A dermoscopic photograph of a skin lesion.
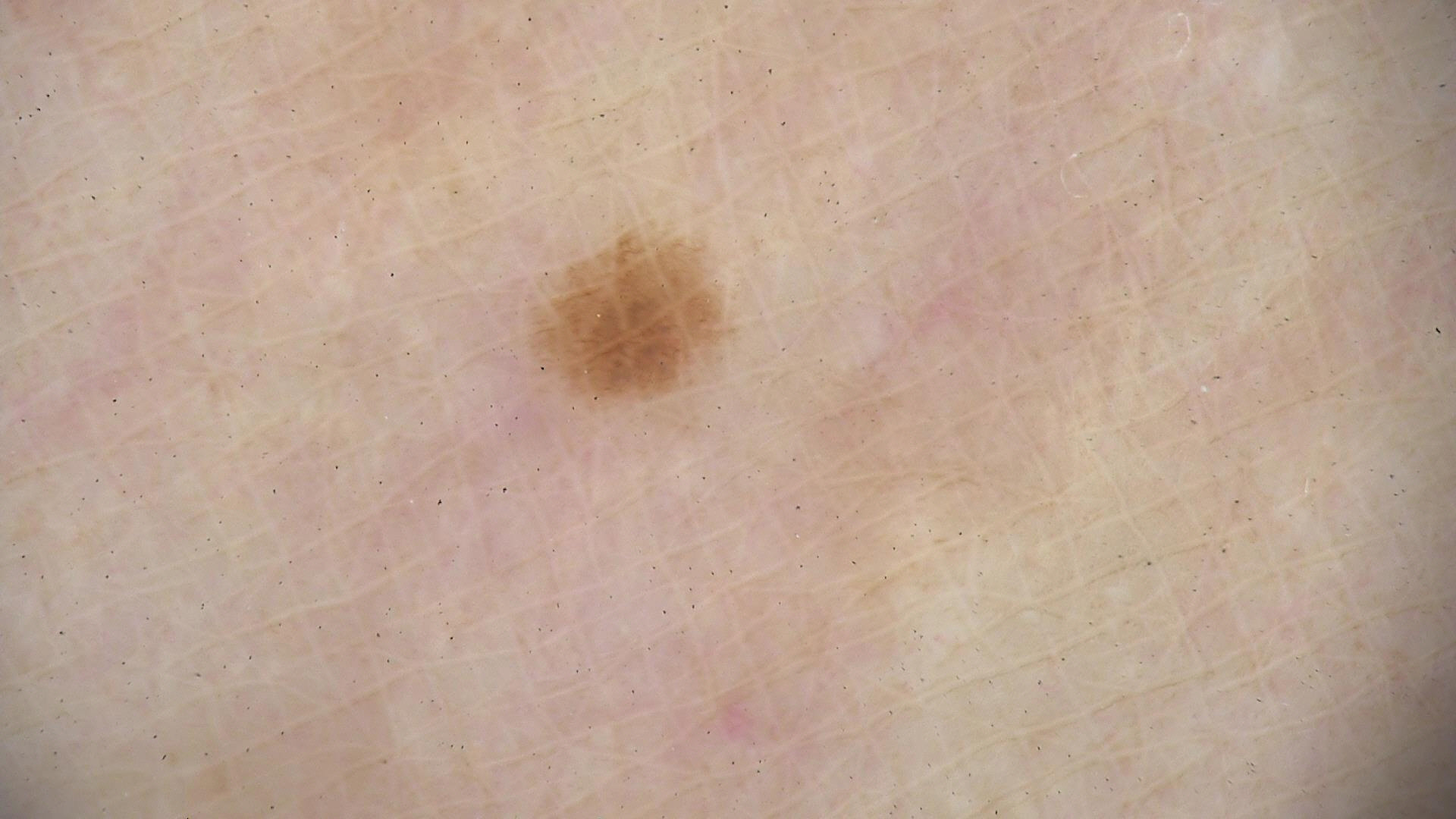subtype: banal
diagnostic label: acral junctional nevus (expert consensus)